Close-up view · present for less than one week · the patient indicates the lesion is raised or bumpy.
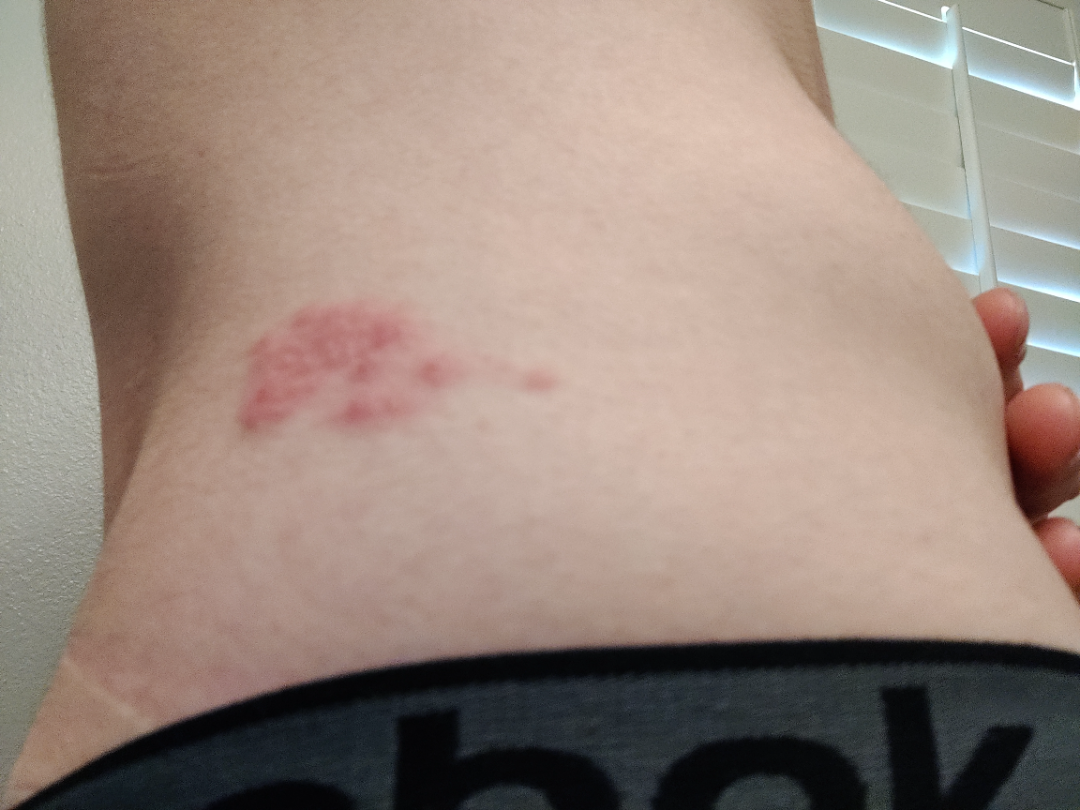A single dermatologist reviewed the case: consistent with Herpes Zoster.